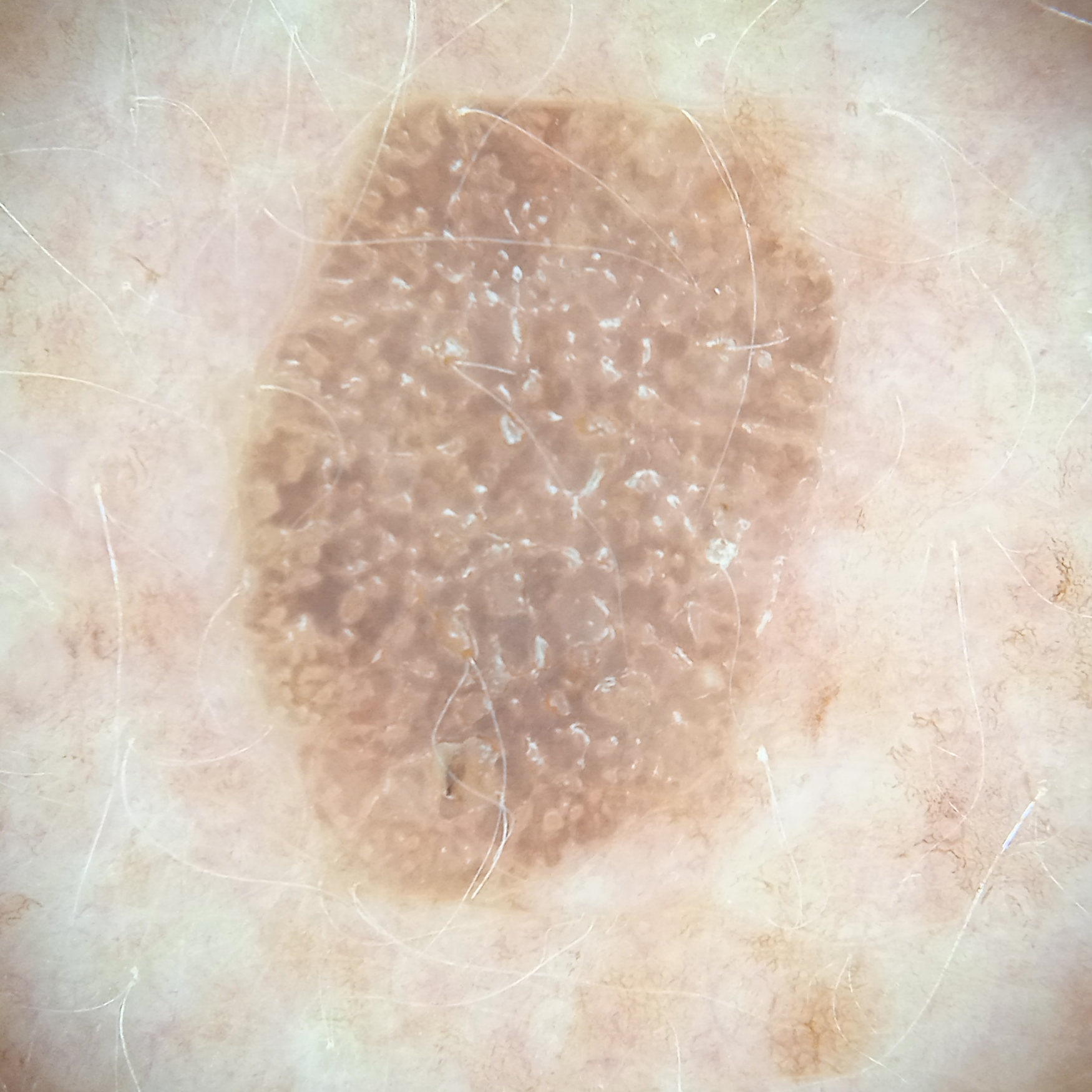Case:
- nevus count: numerous melanocytic nevi
- patient: female, age 78
- sun reaction: skin tans without first burning
- image: dermoscopic image
- referral context: research study (no referral diagnosis)
- diameter: 9.6 mm
- diagnosis: seborrheic keratosis (dermatologist consensus)